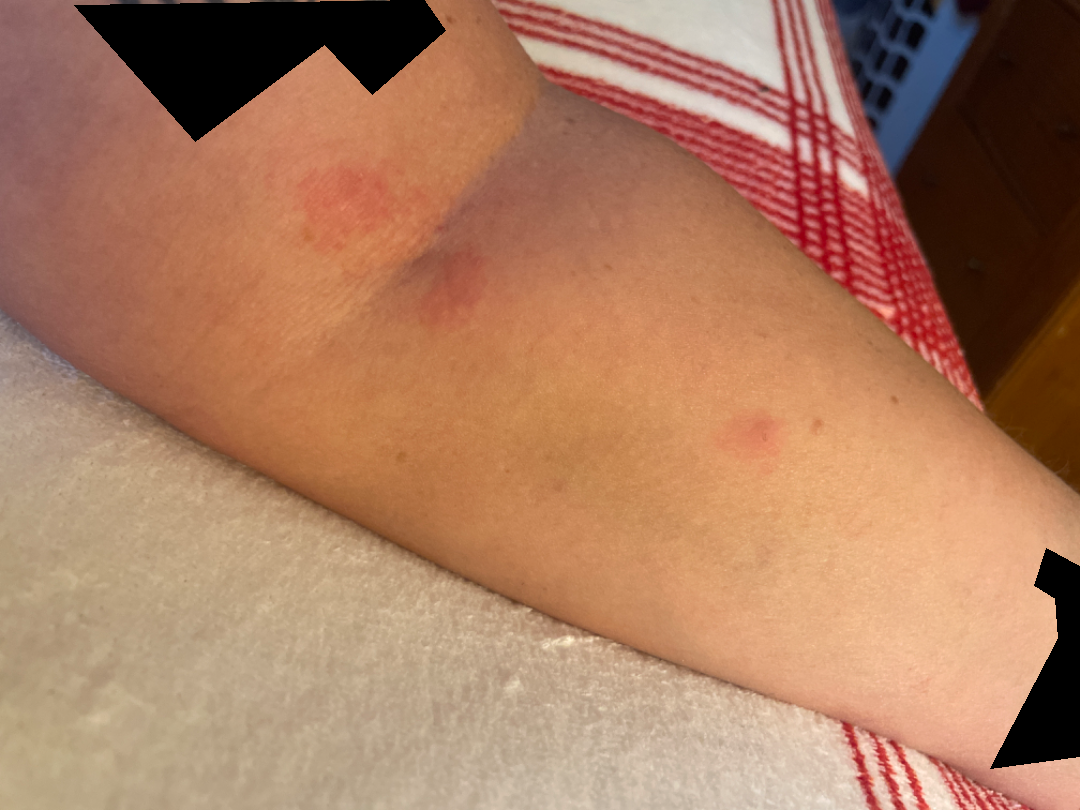history = one to four weeks | described texture = raised or bumpy | image framing = at an angle | dermatologist impression = Eczema (most likely).